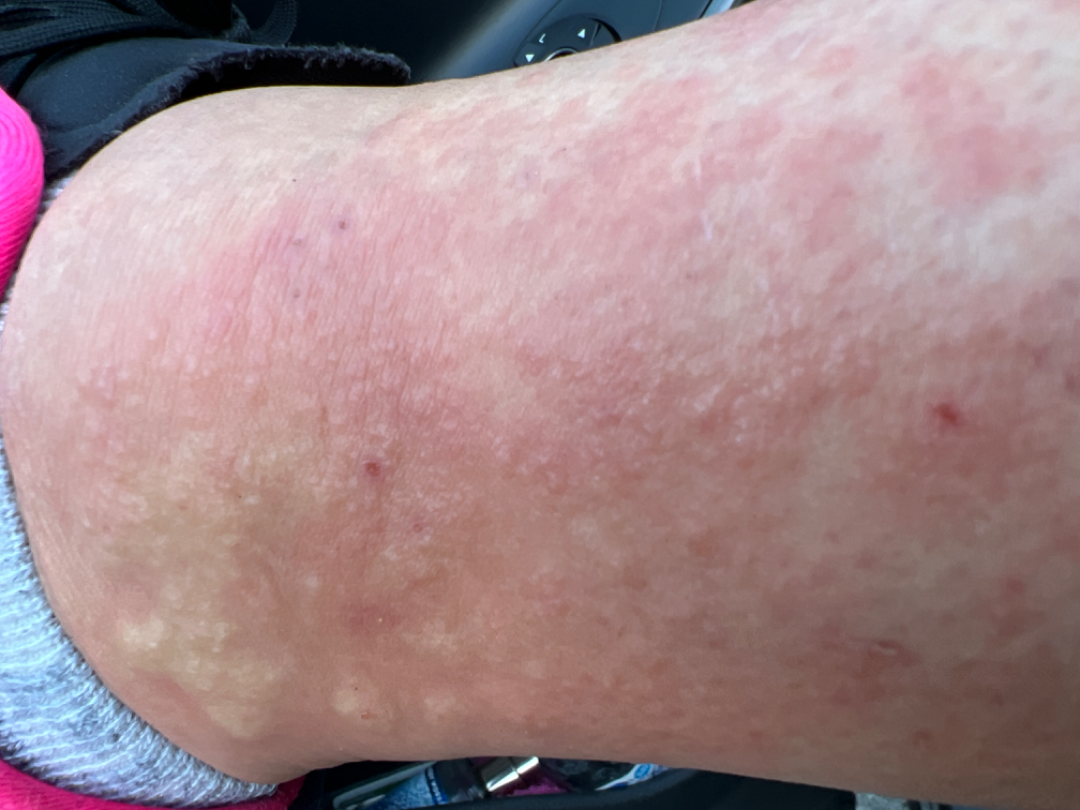History: The lesion involves the leg. The contributor is a female aged 30–39. A close-up photograph. Impression: Eczema (leading); Psoriasis (considered).